The photograph is a close-up of the affected area — 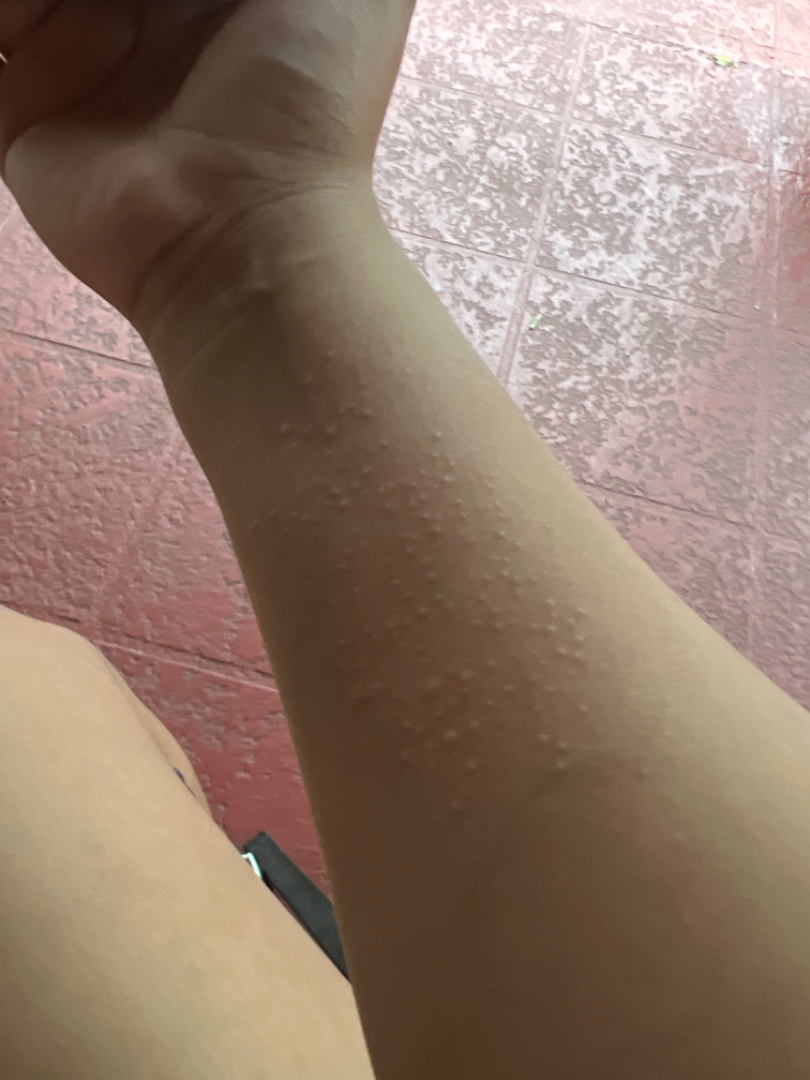<dermatology_case>
  <differential>
    <leading>Lichen nitidus</leading>
    <considered>Miliaria, Allergic Contact Dermatitis</considered>
  </differential>
</dermatology_case>